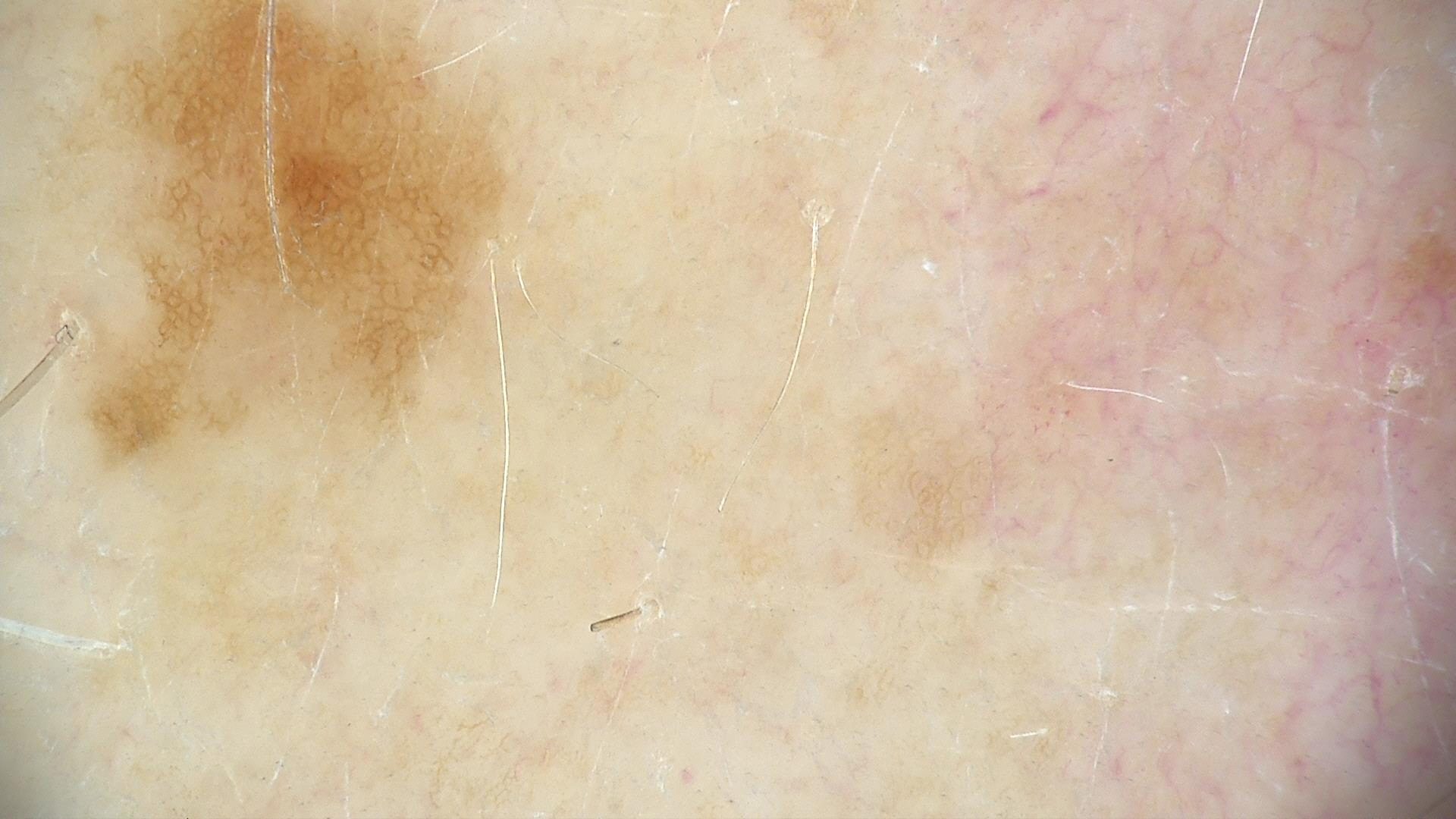modality: dermatoscopy | classification: banal | label: junctional nevus (expert consensus).